A dermoscopic photograph of a skin lesion.
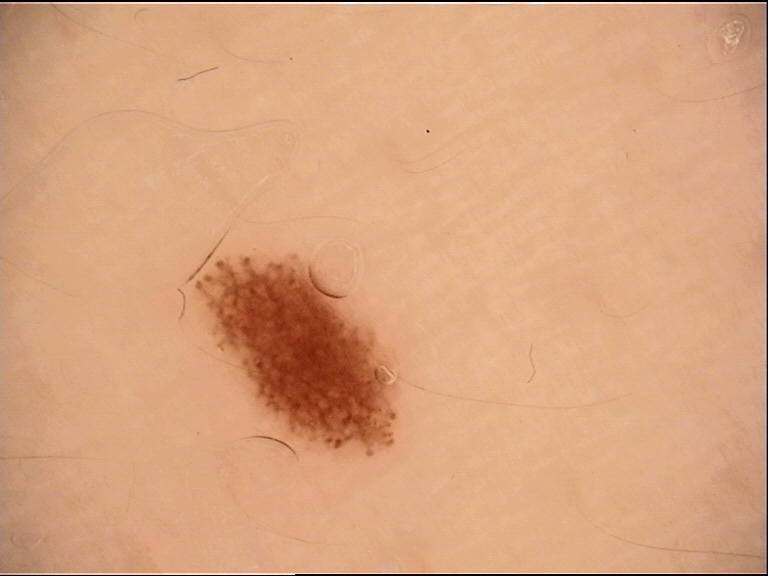| field | value |
|---|---|
| assessment | dysplastic junctional nevus (expert consensus) |